Located on the back of the hand, arm and front of the torso; close-up view.
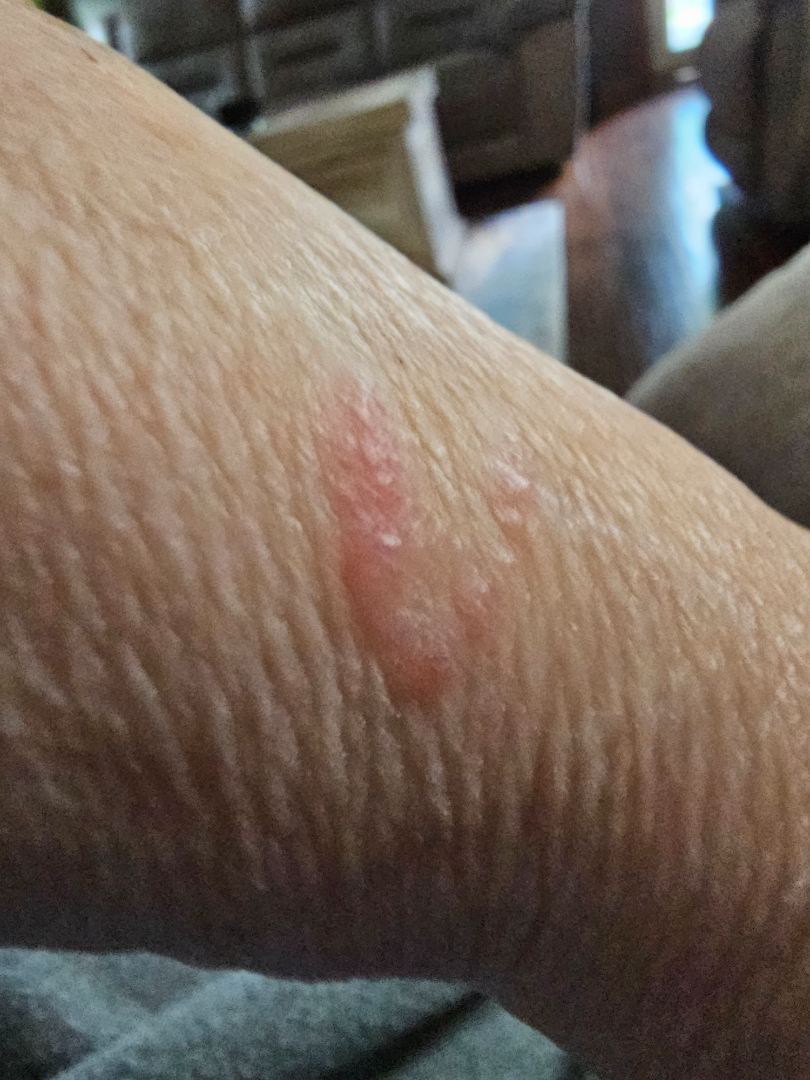The image was not sufficient for the reviewer to characterize the skin condition. The patient indicates itching. Self-categorized by the patient as a rash.